Close-up view.
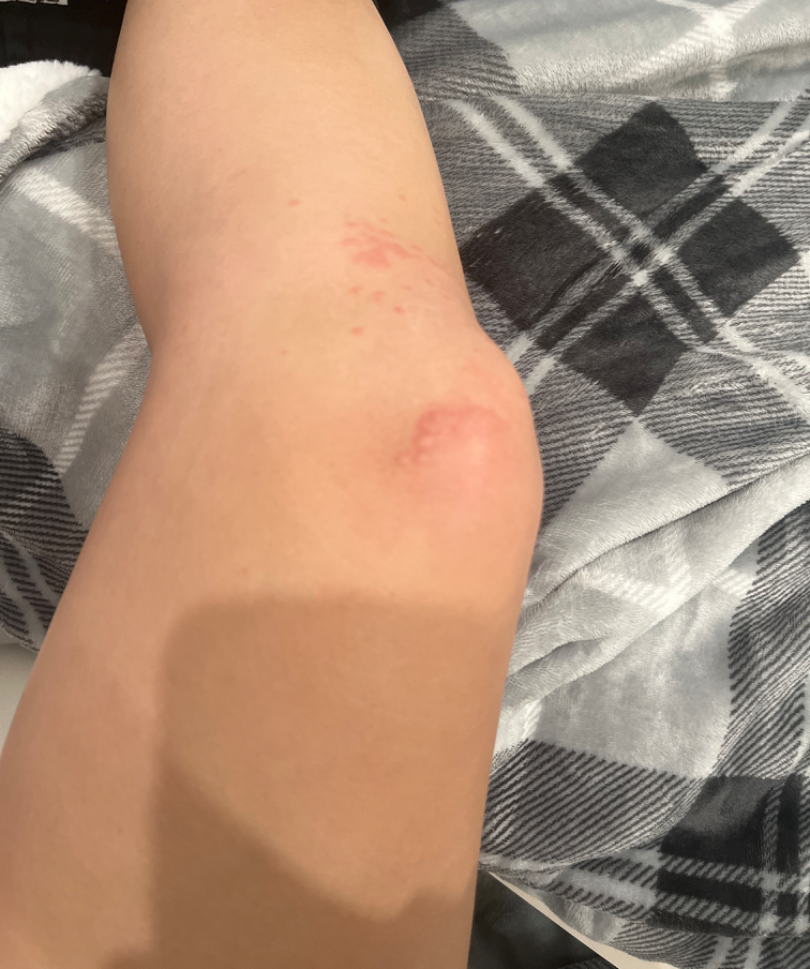The skin findings could not be characterized from the image.